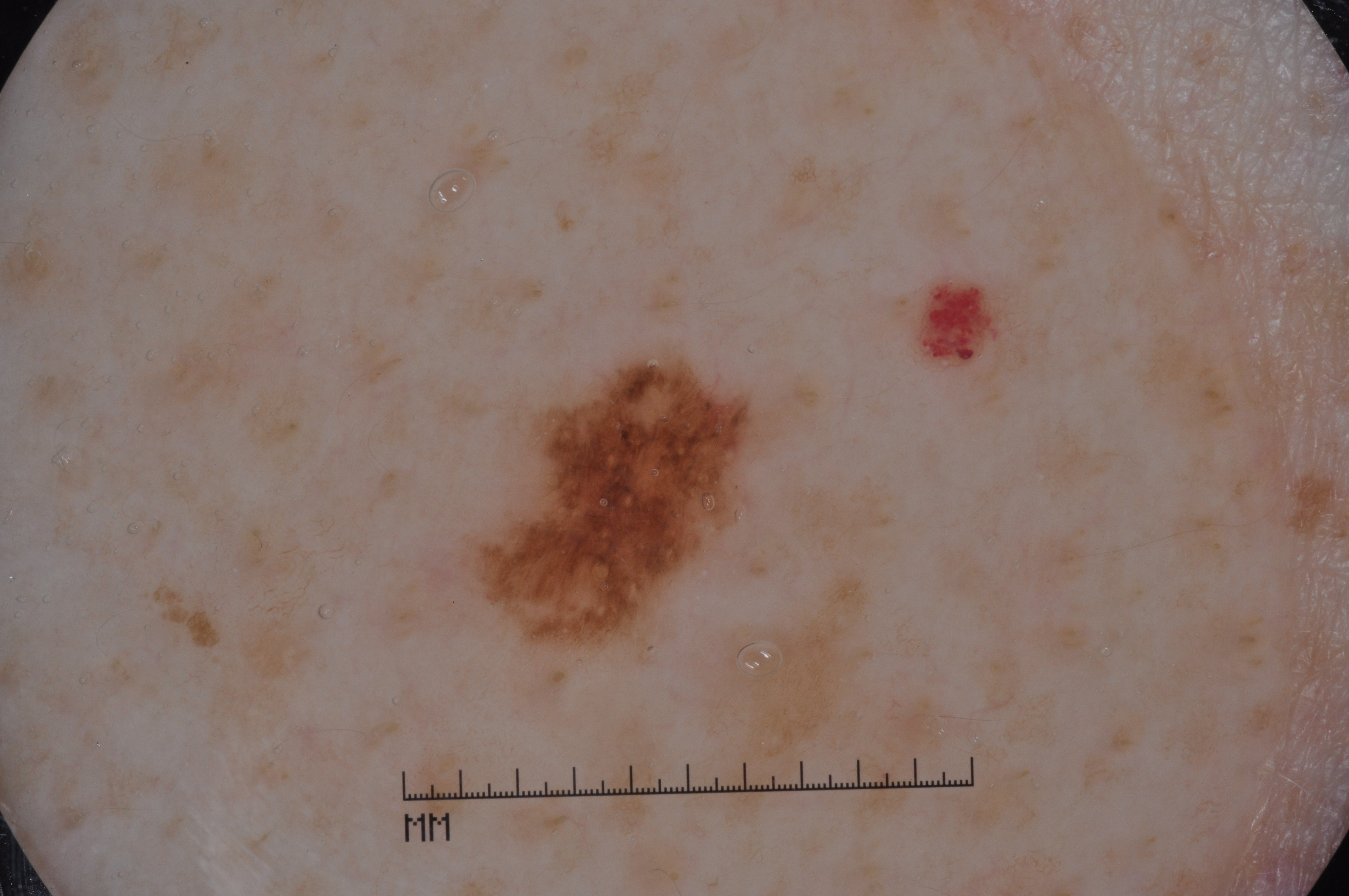Q: What is the imaging modality?
A: dermoscopy
Q: Who is the patient?
A: male, aged approximately 45
Q: How much of the field does the lesion occupy?
A: ~4% of the field
Q: What is the lesion's bounding box?
A: bbox(474, 365, 759, 644)
Q: What dermoscopic features are not present?
A: pigment network, streaks, milia-like cysts, and negative network
Q: What is this lesion?
A: a melanocytic nevus, a benign skin lesion